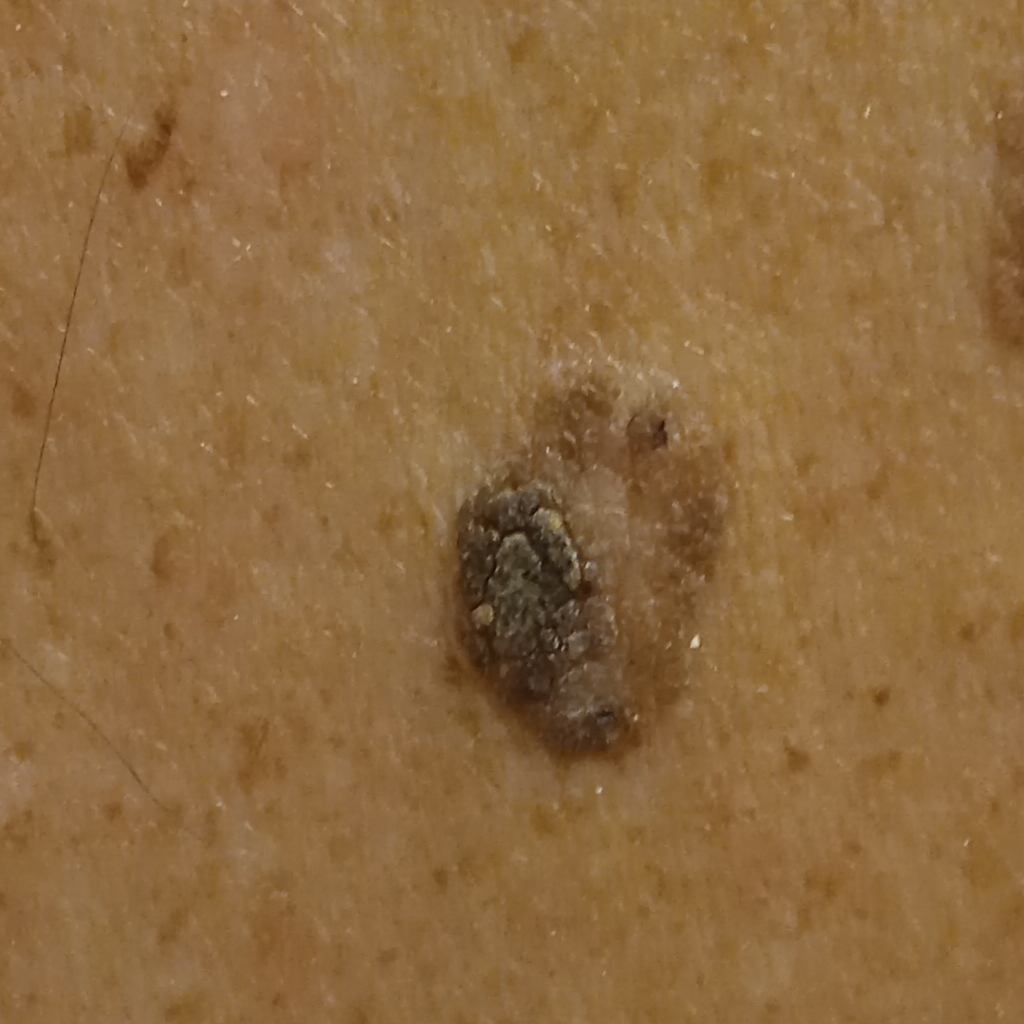patient: male, age 72; risk factors: a personal history of cancer; referral: research study (no referral diagnosis); nevus count: few melanocytic nevi overall; diagnostic label: seborrheic keratosis (dermatologist consensus).